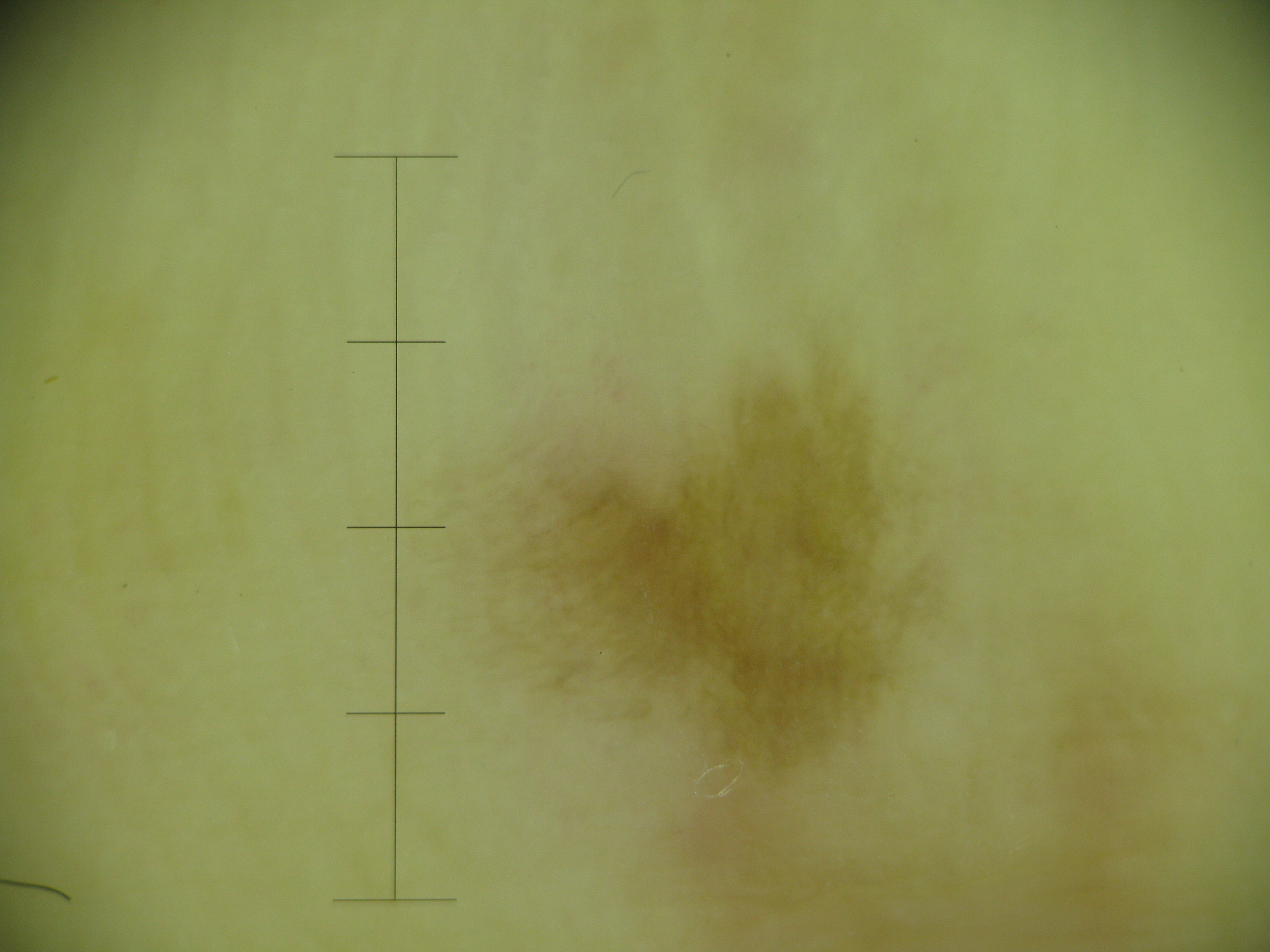Conclusion: Labeled as an acral junctional nevus.